A clinical close-up photograph of a skin lesion. The chart notes alcohol use, prior malignancy (patient or family), and no prior skin cancer (patient or family). Fitzpatrick IV. A female subject age 37: 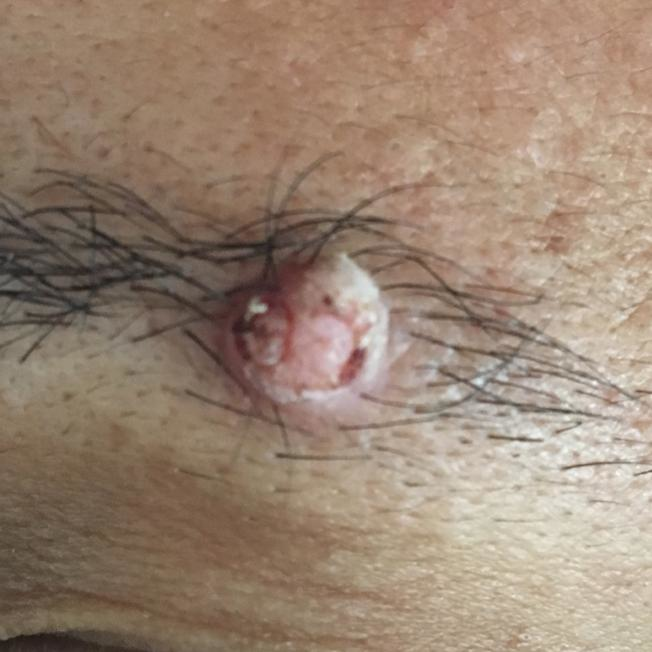Patient and lesion: The lesion is located on the face. The lesion is roughly 8 by 7 mm. Per patient report, the lesion itches, is elevated, has grown, and has bled, but has not changed and does not hurt. Conclusion: The biopsy diagnosis was a lesion with uncertain malignant potential — an actinic keratosis.